The subject is 18–29, female. This image was taken at an angle. The affected area is the arm — 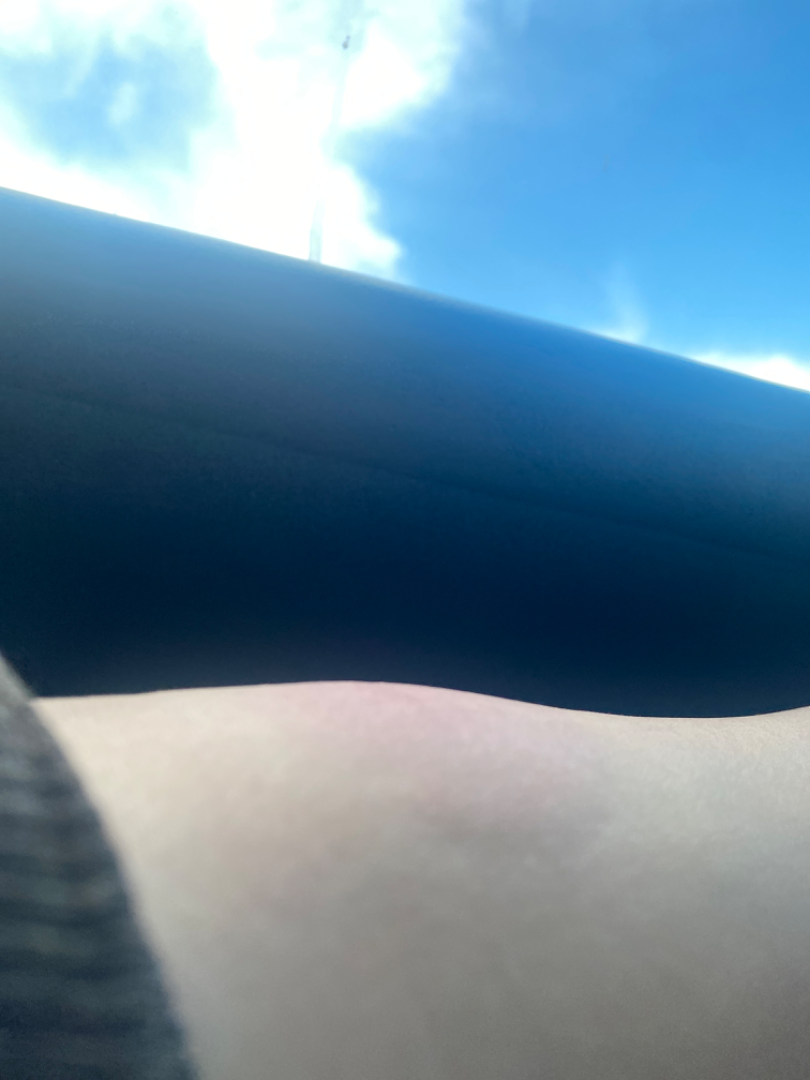differential:
  leading:
    - Insect Bite
  considered:
    - Erythema annulare centrifugum